The patient is a male roughly 50 years of age · a dermoscopy image of a single skin lesion:
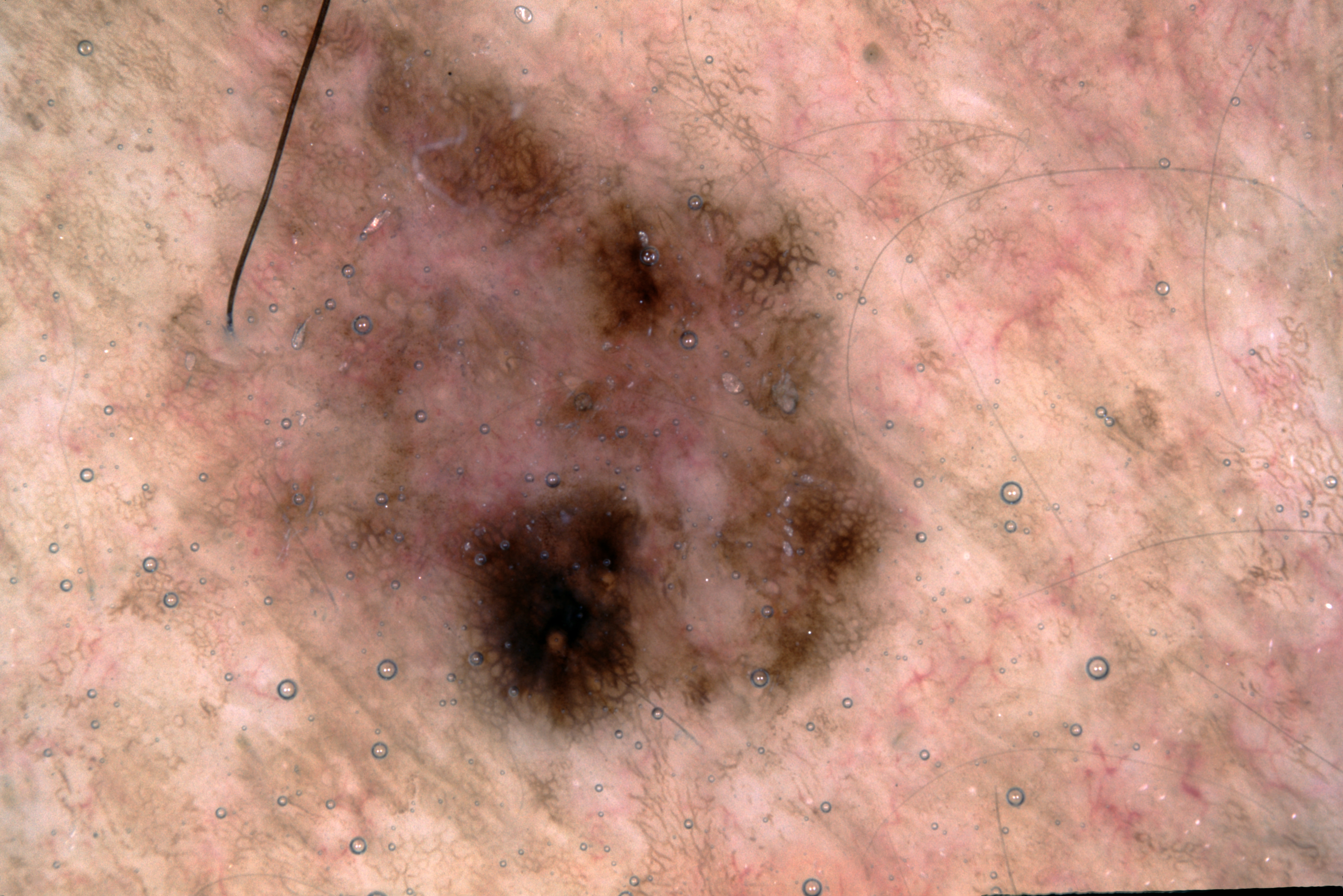{
  "dermoscopic_features": {
    "present": [
      "pigment network"
    ],
    "absent": [
      "negative network",
      "milia-like cysts",
      "streaks"
    ]
  },
  "lesion_location": {
    "bbox_xyxy": [
      55,
      0,
      975,
      895
    ]
  },
  "diagnosis": {
    "name": "melanoma",
    "malignancy": "malignant",
    "lineage": "melanocytic",
    "provenance": "histopathology"
  }
}